This image was taken at an angle; the lesion involves the top or side of the foot, arm and back of the hand:
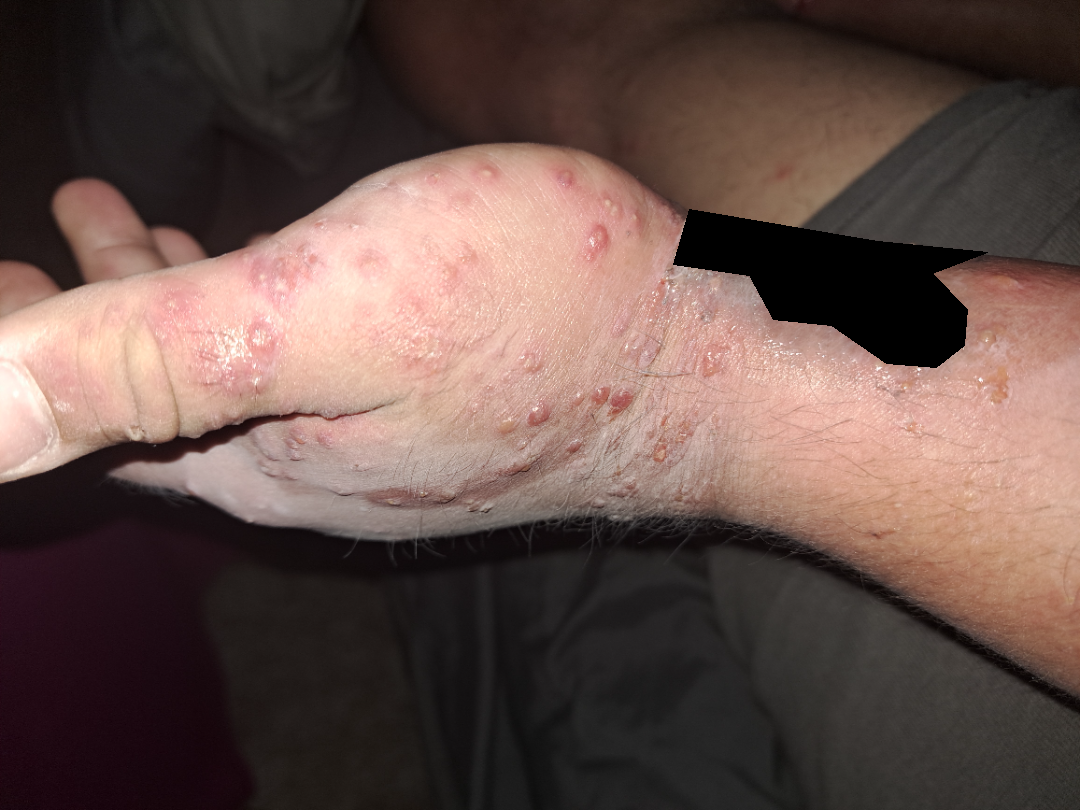Reported lesion symptoms include pain, bothersome appearance, burning, enlargement and itching. Present for about one day. Texture is reported as fluid-filled, raised or bumpy and rough or flaky. Self-categorized by the patient as a rash. Associated systemic symptoms include fatigue and chills. On photographic review: Contact dermatitis (weight 0.35); Allergic Contact Dermatitis (weight 0.22); Insect Bite (weight 0.22); Acute generalised exanthematous pustulosis (weight 0.22).